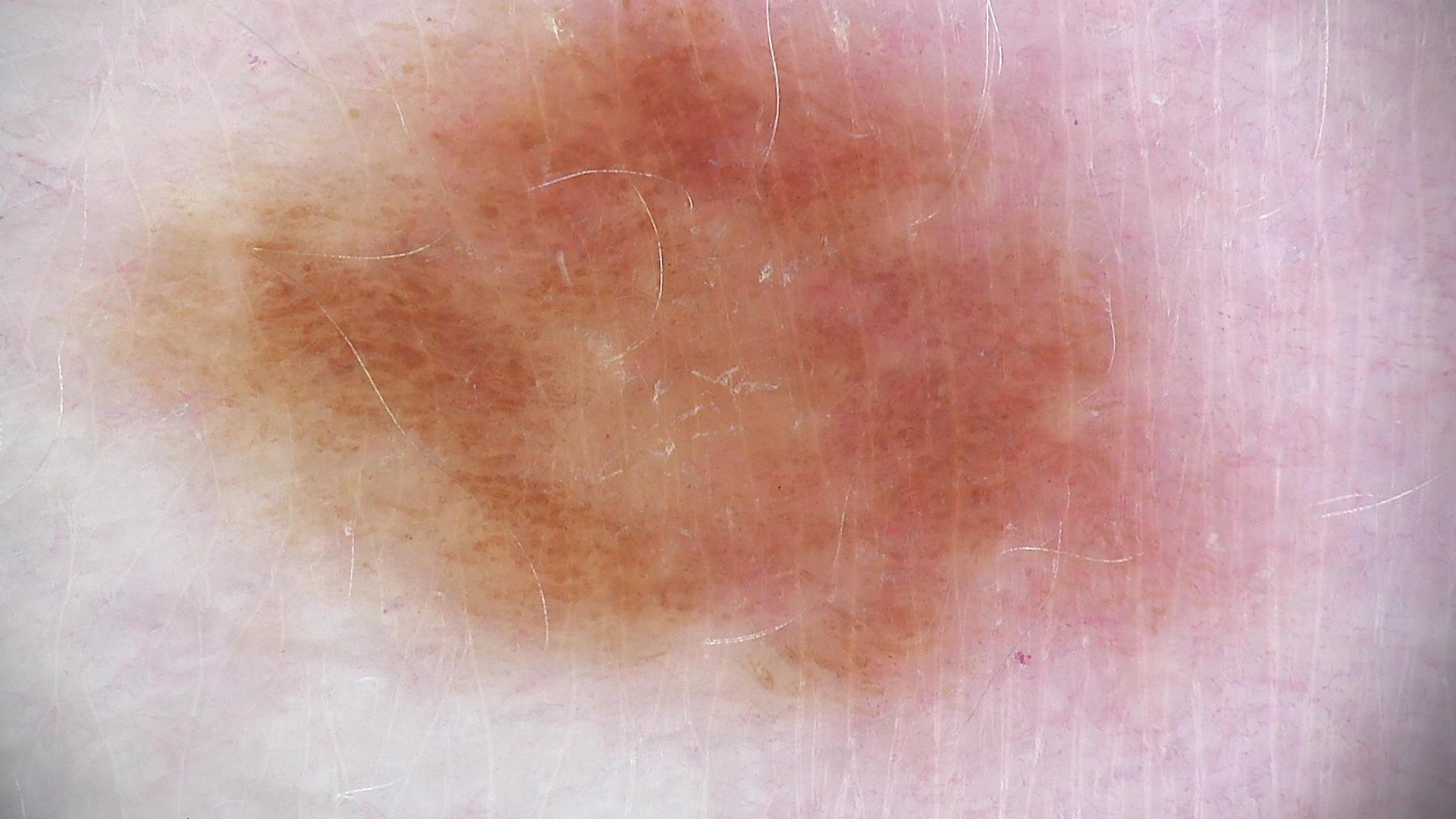image type — dermoscopy; diagnosis — dysplastic junctional nevus (expert consensus).